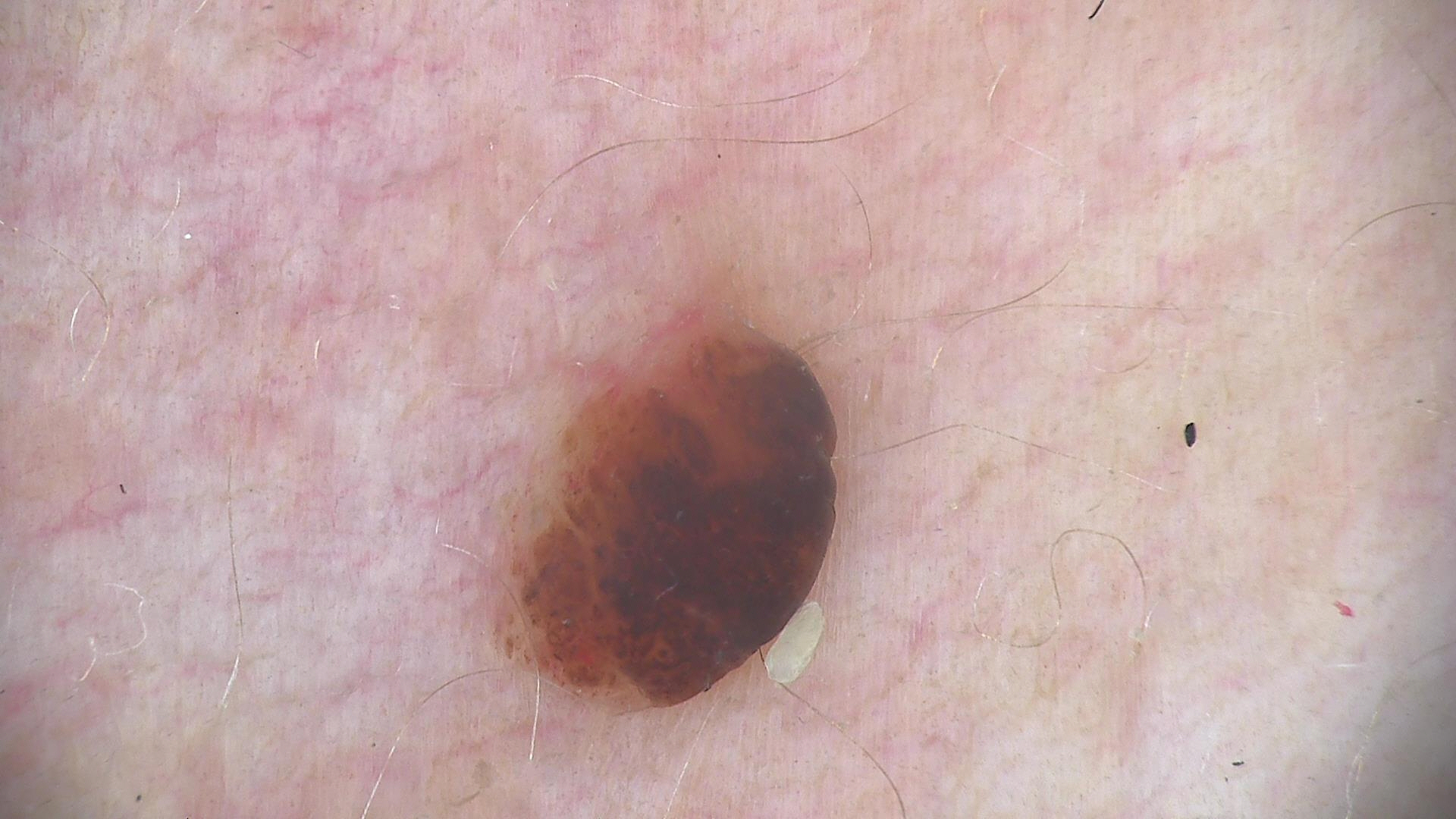Summary: Dermoscopy of a skin lesion. Impression: Labeled as a banal lesion — a dermal nevus.